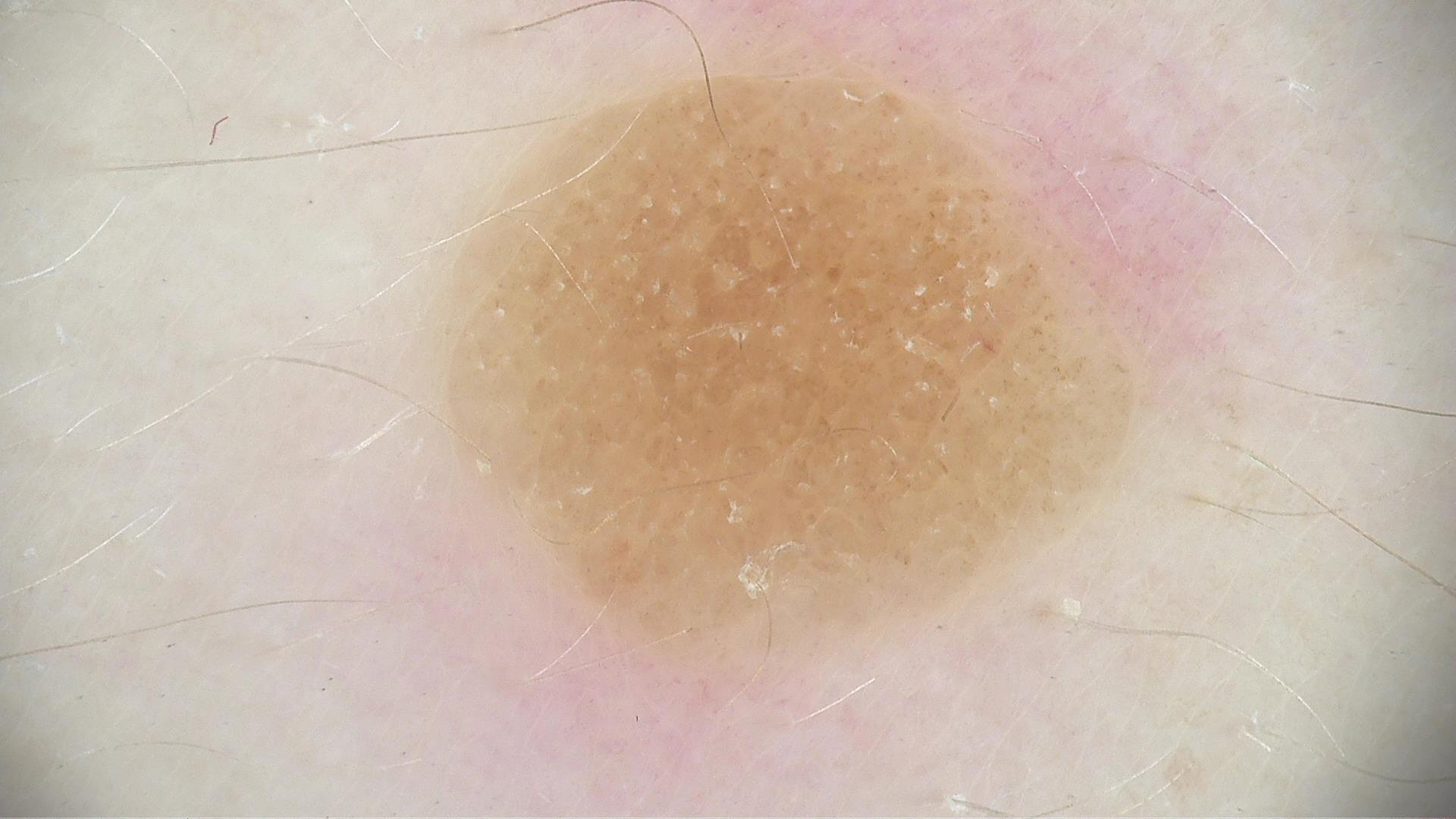A dermoscopic close-up of a skin lesion.
The diagnosis was a banal lesion — a dermal nevus.